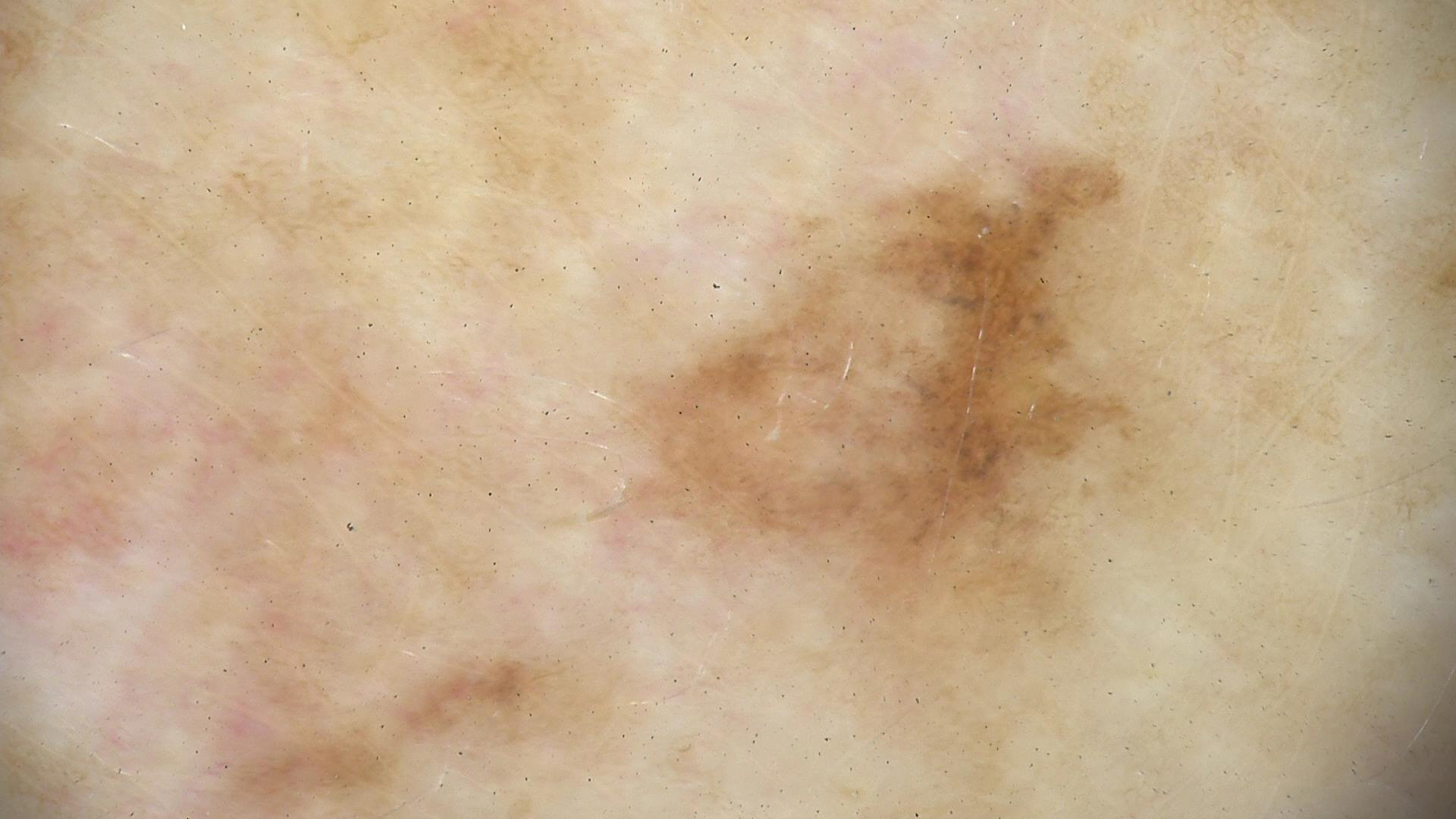The biopsy diagnosis was a melanoma.